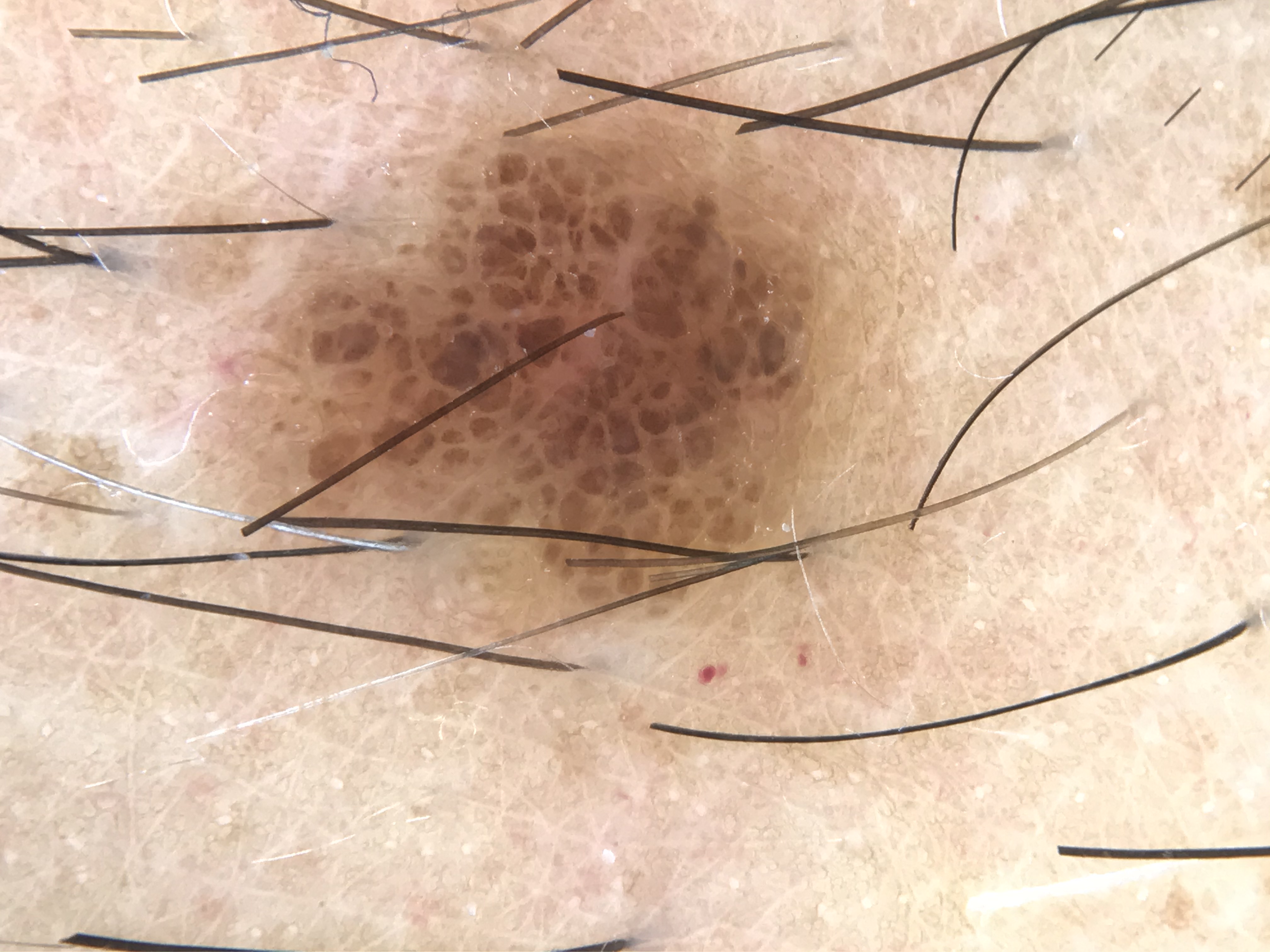imaging: dermatoscopy, classification: banal, class: compound nevus (expert consensus).